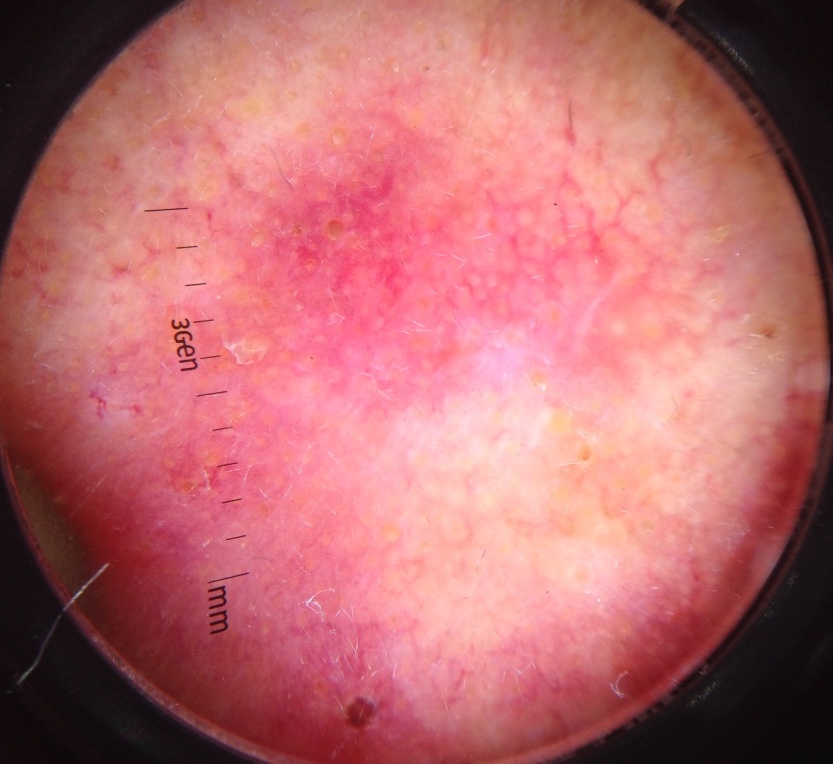A skin lesion imaged with a dermatoscope. The diagnostic label was a keratinocytic lesion — an actinic keratosis.